By history, tobacco use, alcohol use, and no pesticide exposure. The patient was assessed as FST I: 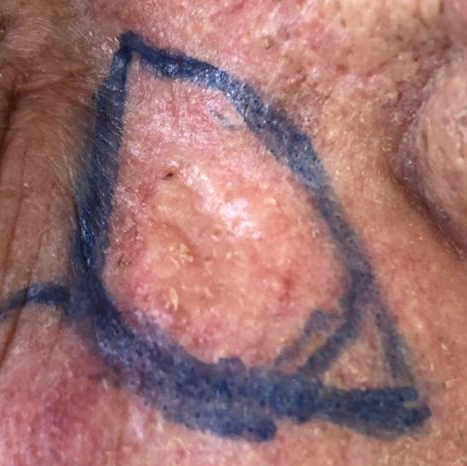| key | value |
|---|---|
| site | the face |
| diameter | approx. 13 × 10 mm |
| symptoms | itching, elevation / no bleeding |
| diagnostic label | basal cell carcinoma (biopsy-proven) |